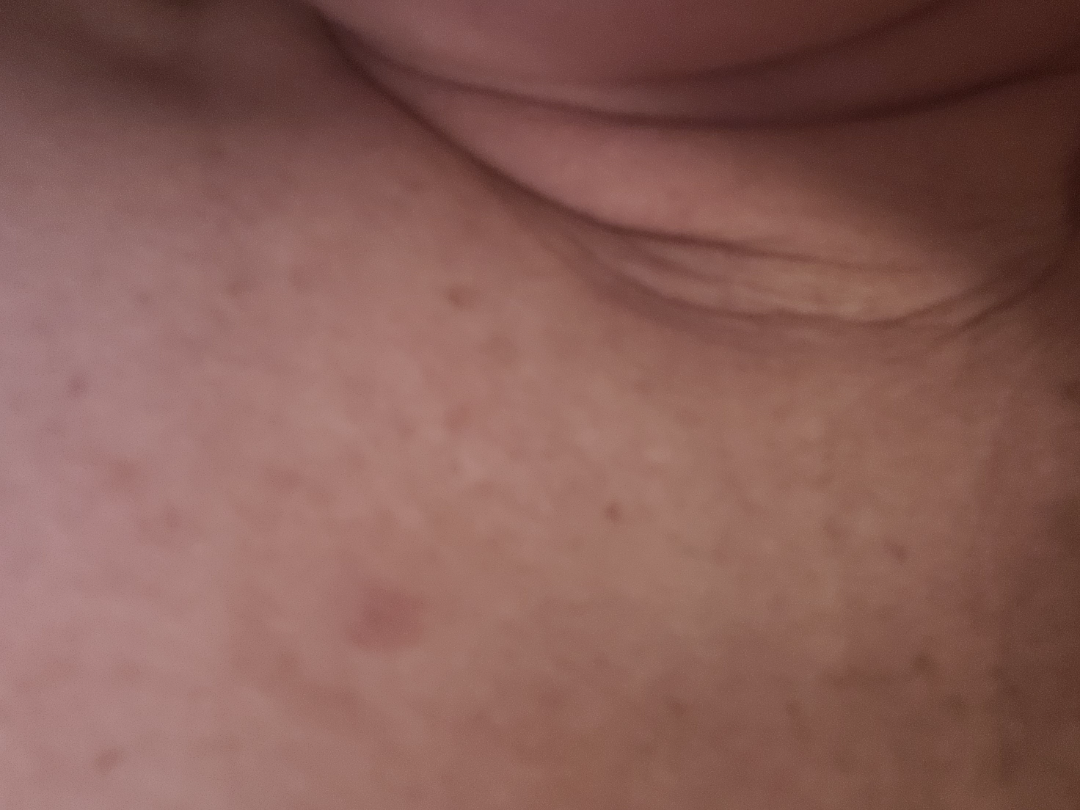| feature | finding |
|---|---|
| assessment | ungradable on photographic review |